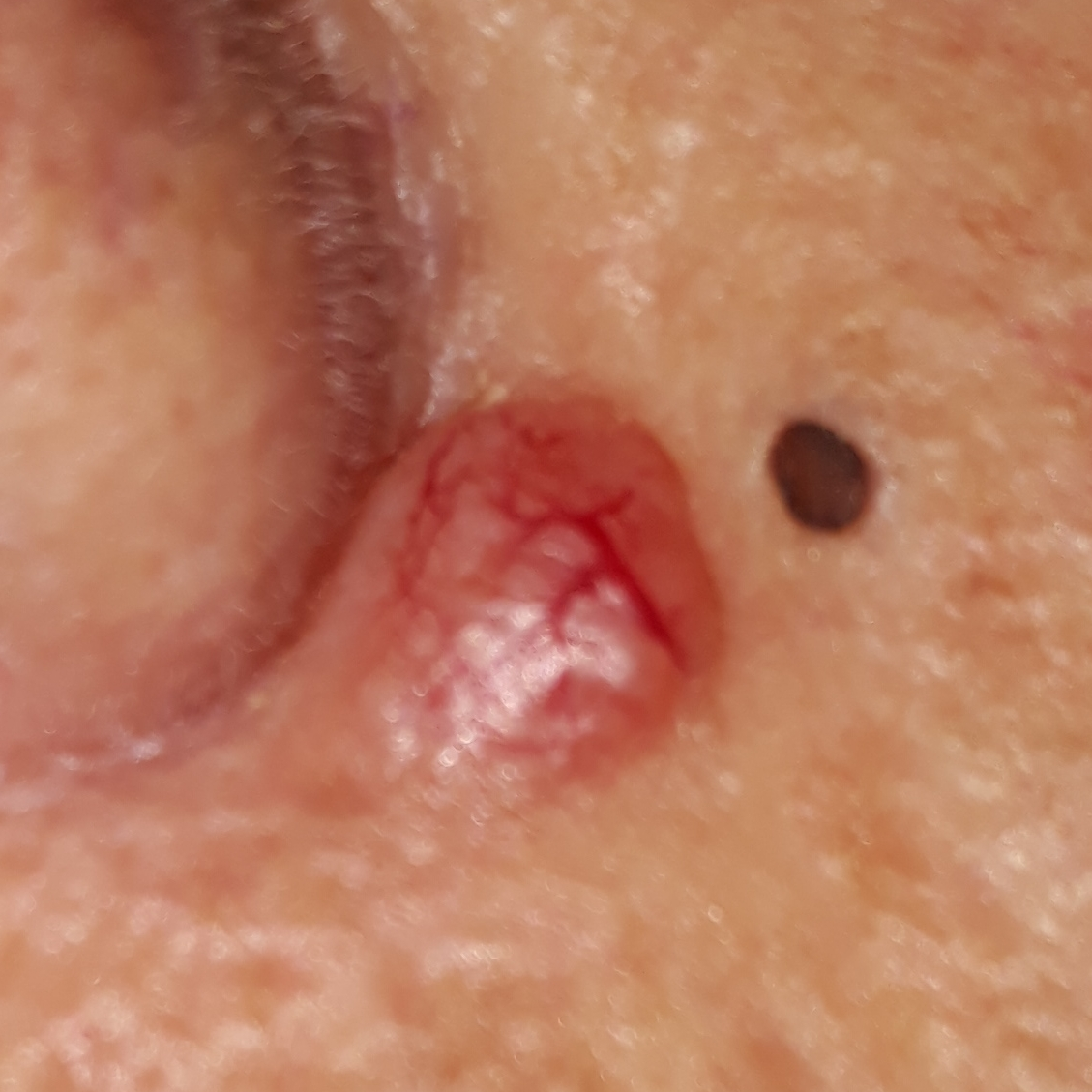Q: Tell me about the patient.
A: female, age 78
Q: What is the imaging modality?
A: smartphone clinical photo
Q: Where on the body is the lesion?
A: the face
Q: Any reported symptoms?
A: itching, elevation, bleeding / no pain, no change in appearance
Q: What did the workup show?
A: basal cell carcinoma (biopsy-proven)